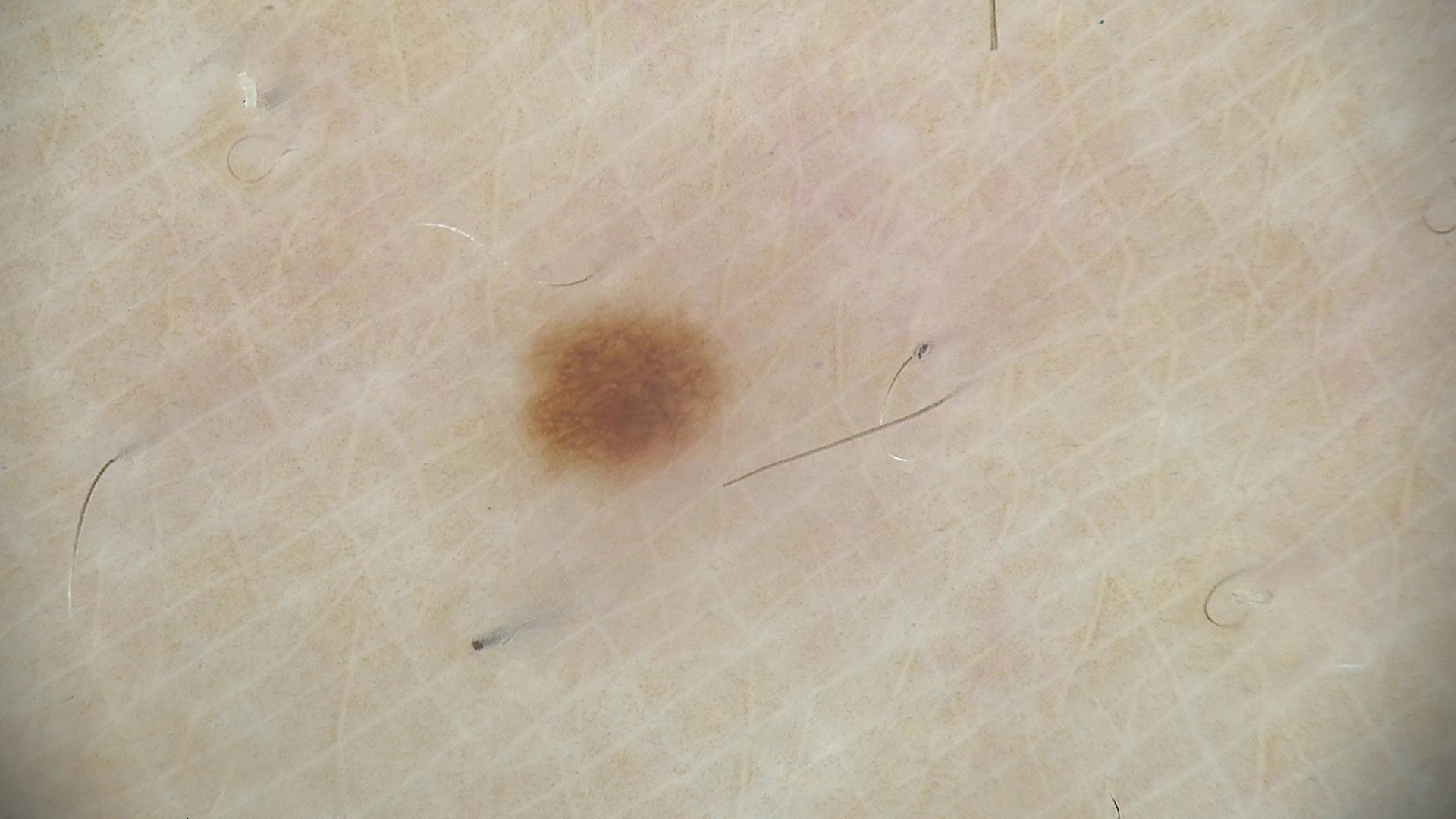Classified as a benign lesion — a dysplastic junctional nevus.